A dermoscopic close-up of a skin lesion.
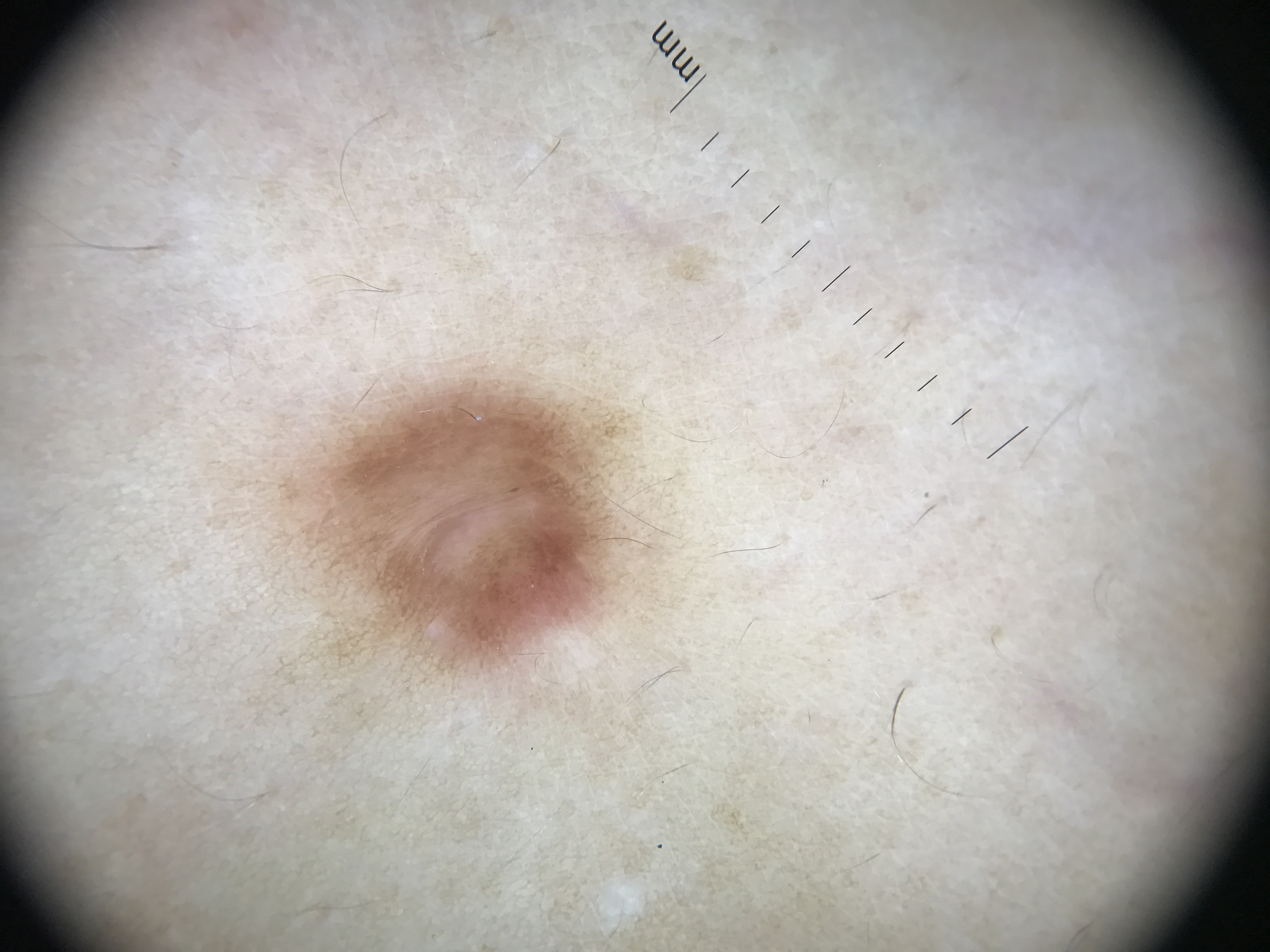diagnosis:
  name: dermatofibroma
  code: df
  malignancy: benign
  super_class: non-melanocytic
  confirmation: expert consensus